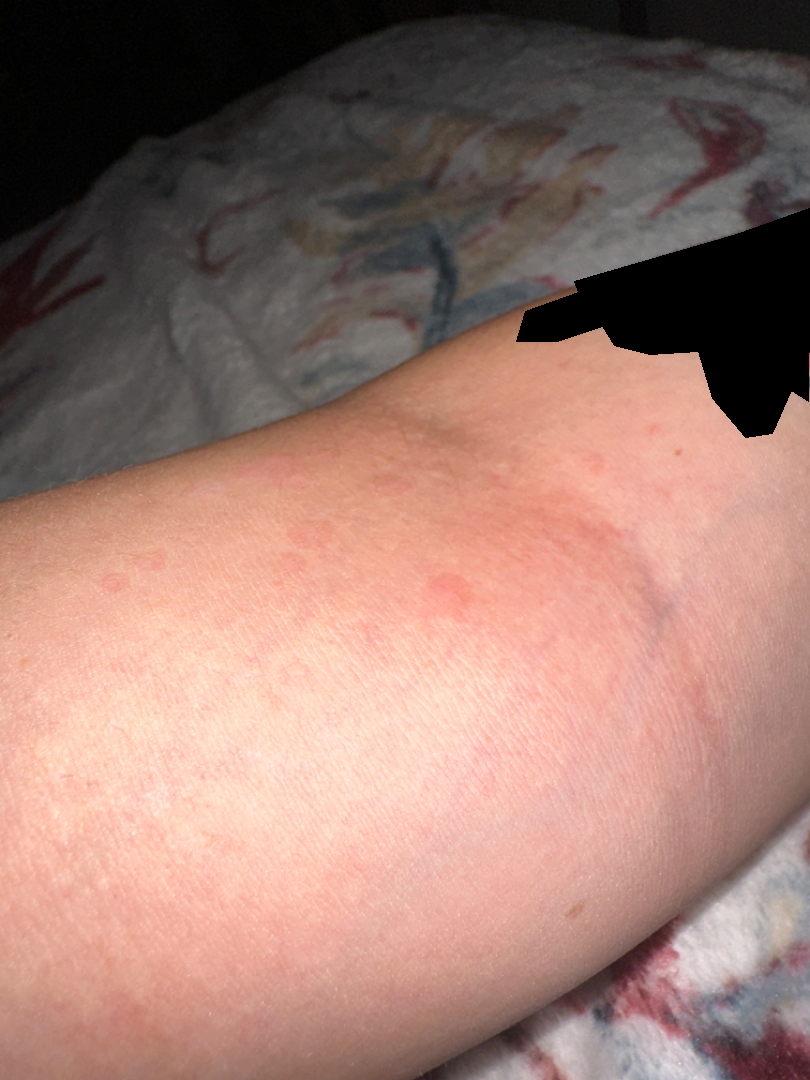Q: Image view?
A: at an angle
Q: Age and sex?
A: female, age 18–29
Q: What is the affected area?
A: arm
Q: What is the dermatologist's impression?
A: the leading impression is Tinea Versicolor; possibly Urticaria; a more distant consideration is Eczema; less likely is Insect Bite; less probable is Psoriasis